A dermoscopy image of a single skin lesion.
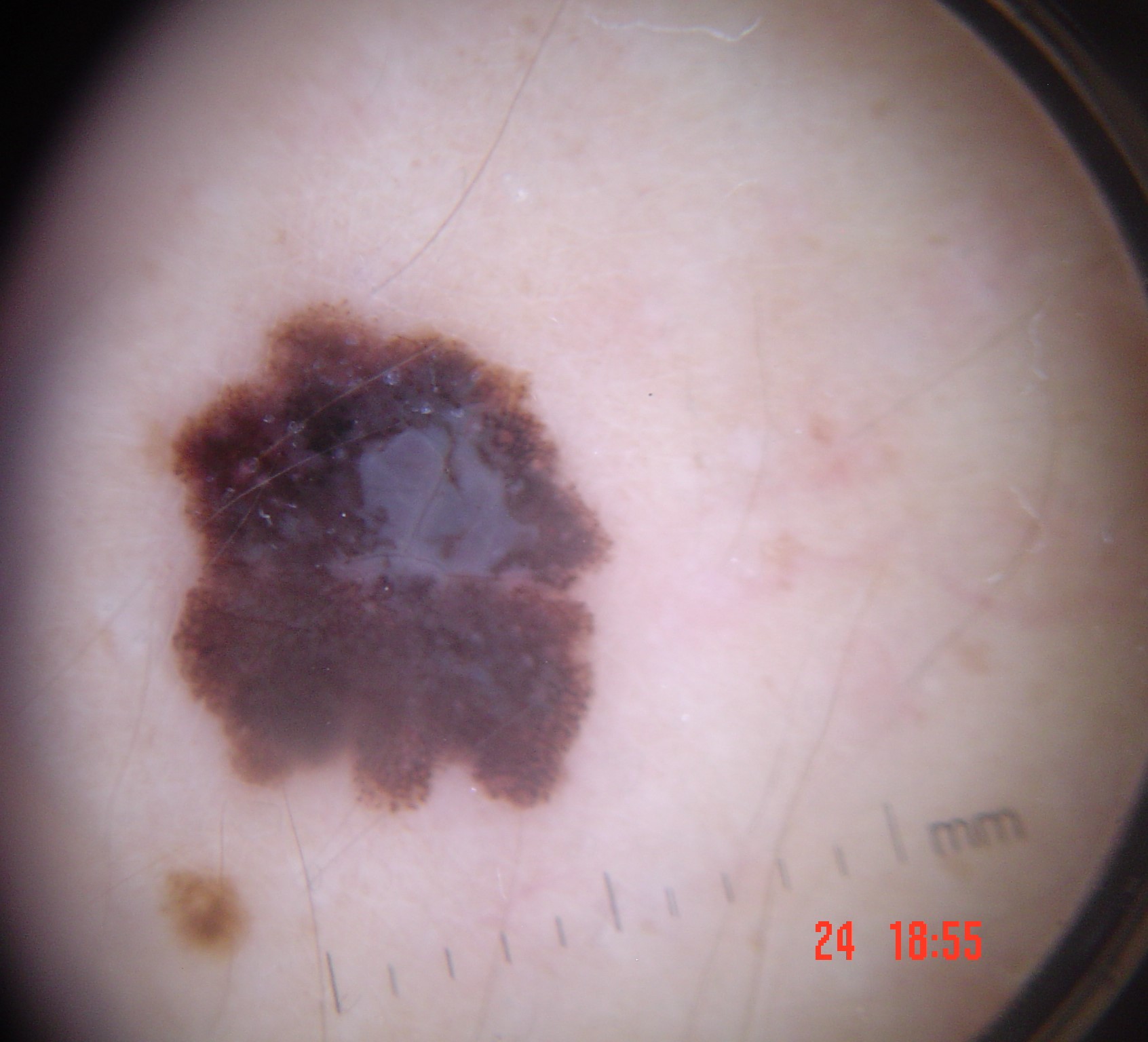The biopsy diagnosis was a melanoma.